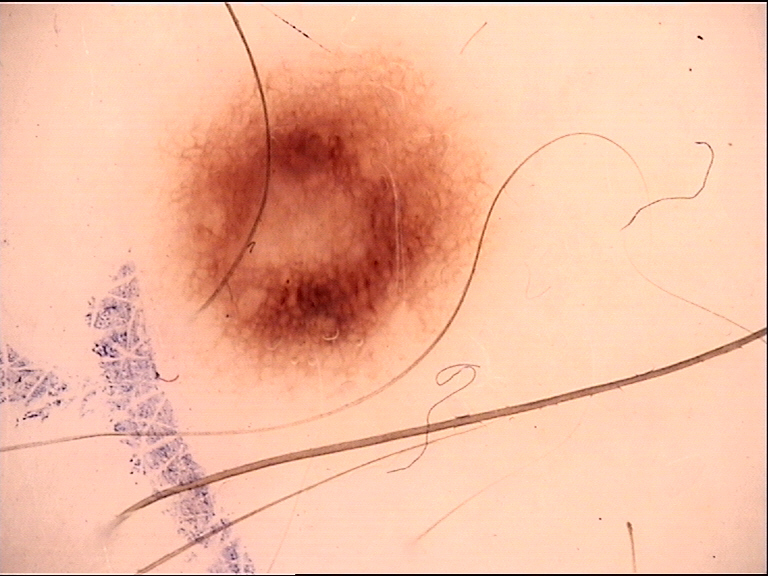The diagnostic label was a dysplastic junctional nevus.